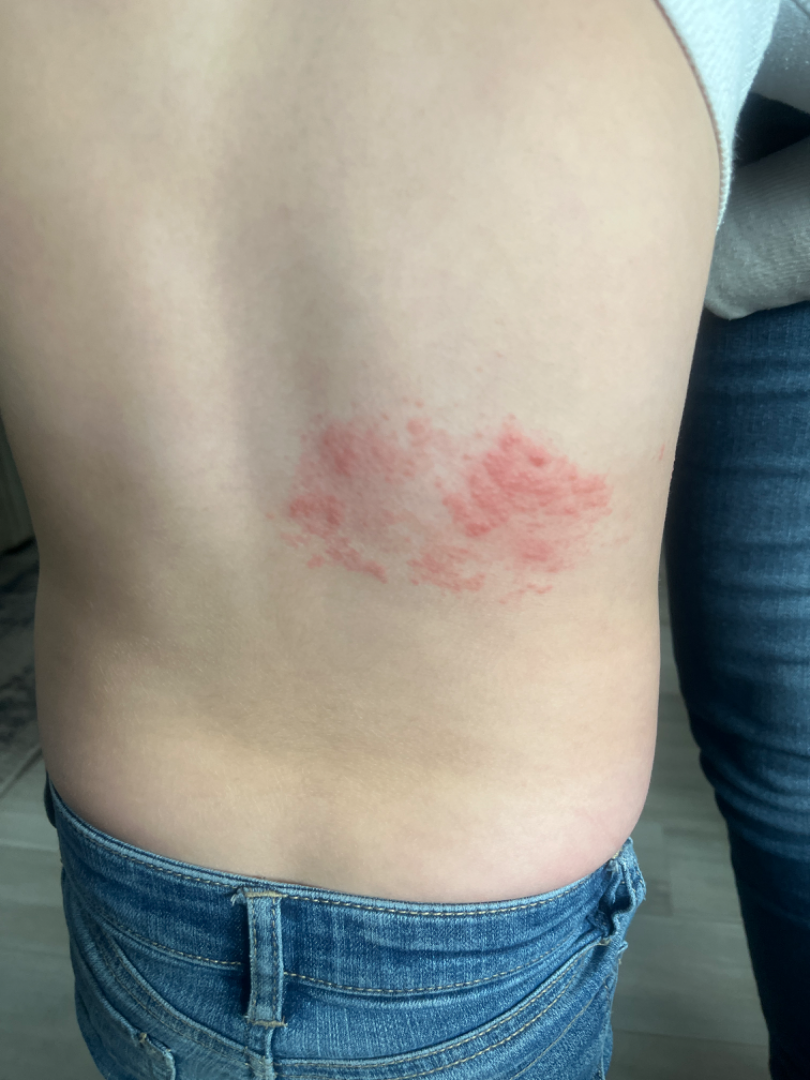History: Skin tone: Fitzpatrick phototype III; non-clinician graders estimated Monk skin tone scale 1 or 2 (two reviewer pools). The photograph is a close-up of the affected area. Impression: The differential is split between Acute dermatitis, NOS; Herpes Zoster; and Allergic Contact Dermatitis.